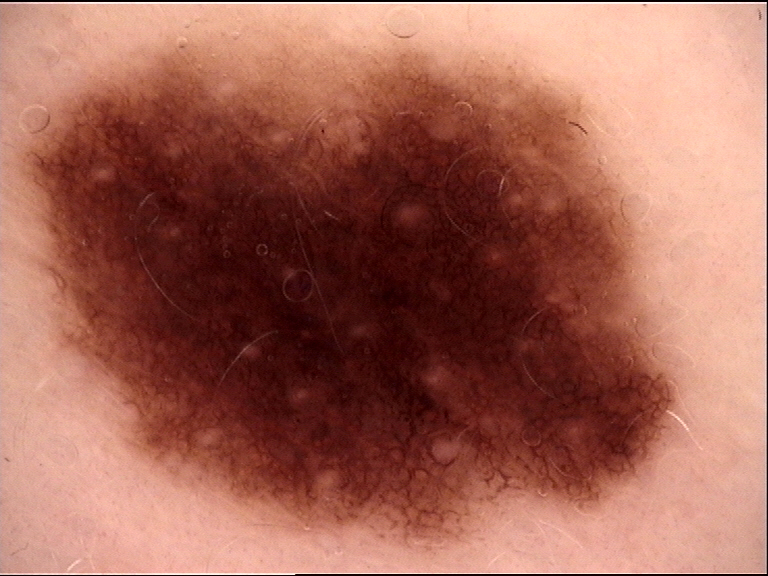* assessment · dysplastic junctional nevus (expert consensus)